The patient indicates the lesion is raised or bumpy. The lesion is associated with itching. No constitutional symptoms were reported. The subject is 40–49, female. Self-categorized by the patient as a rash. The lesion involves the leg and top or side of the foot. This image was taken at an angle.
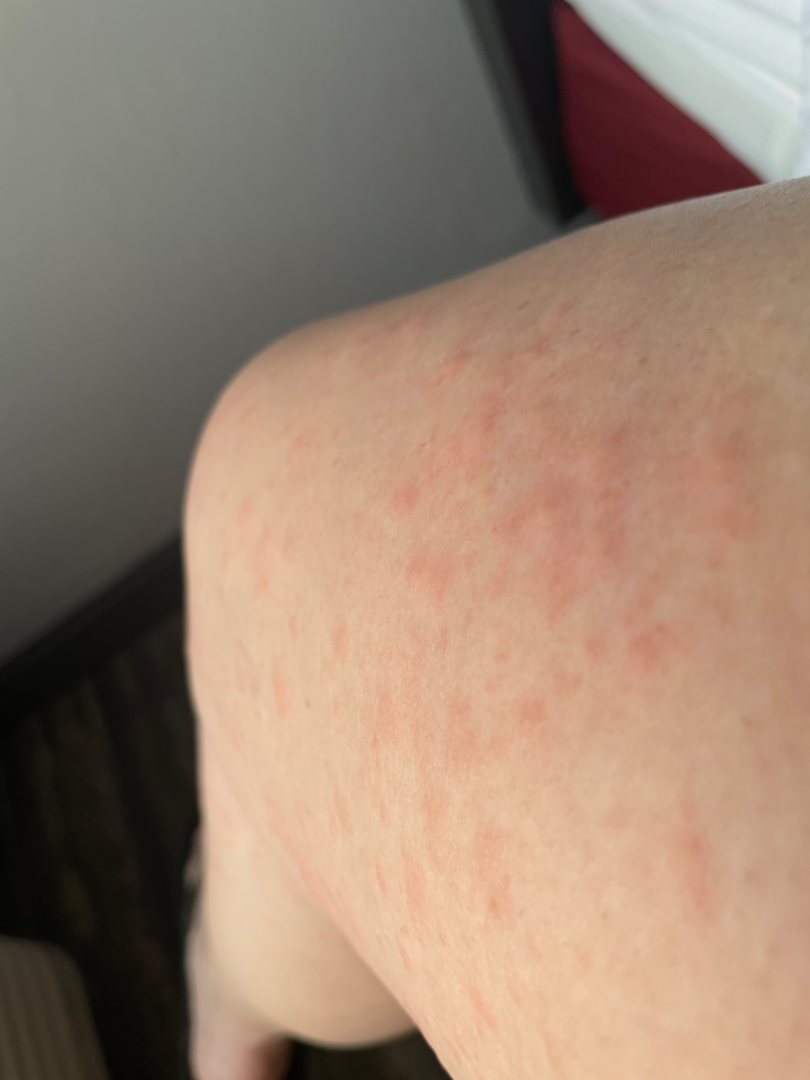Findings:
• clinical impression · the leading consideration is Urticaria; less probable is Eczema; less likely is Allergic Contact Dermatitis; lower on the differential is Viral Exanthem; a remote consideration is Hypersensitivity